Dermoscopy of a skin lesion · the patient is a female aged 43-47:
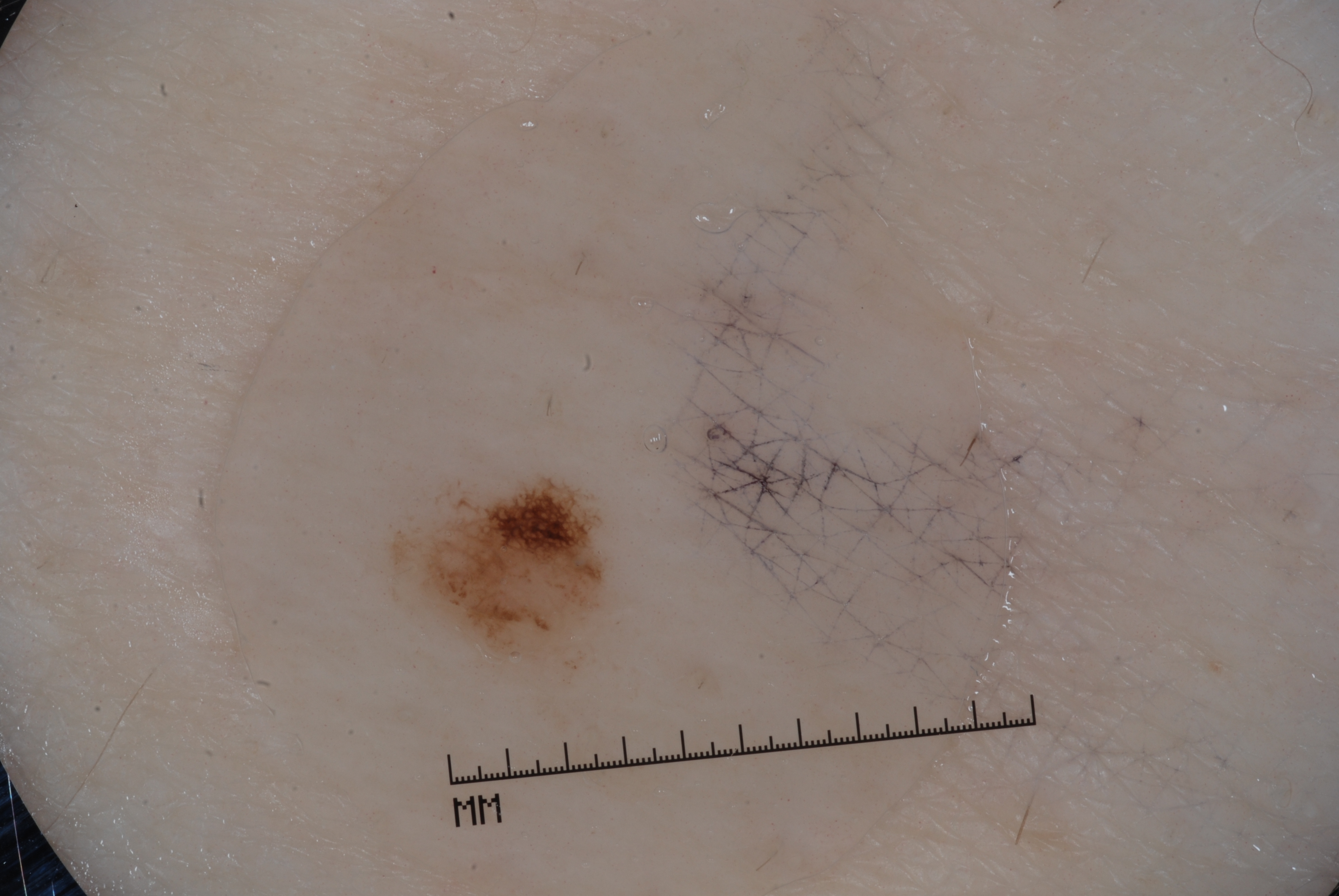Case summary:
A small lesion within a wider field of skin. The visible lesion spans x1=387, y1=483, x2=606, y2=665. The dermoscopic pattern shows pigment network; no streaks, milia-like cysts, or negative network.
Conclusion:
Diagnosed as a melanocytic nevus, a benign skin lesion.